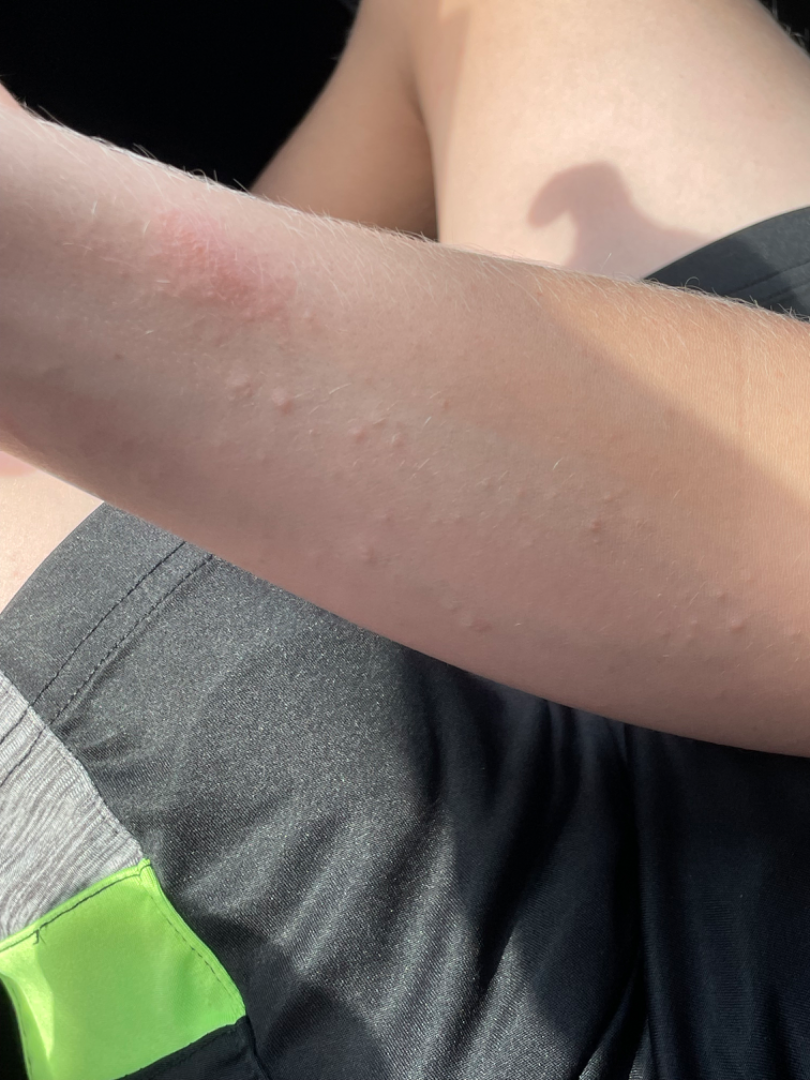Review: Eczema (0.50); Acute dermatitis, NOS (0.50).